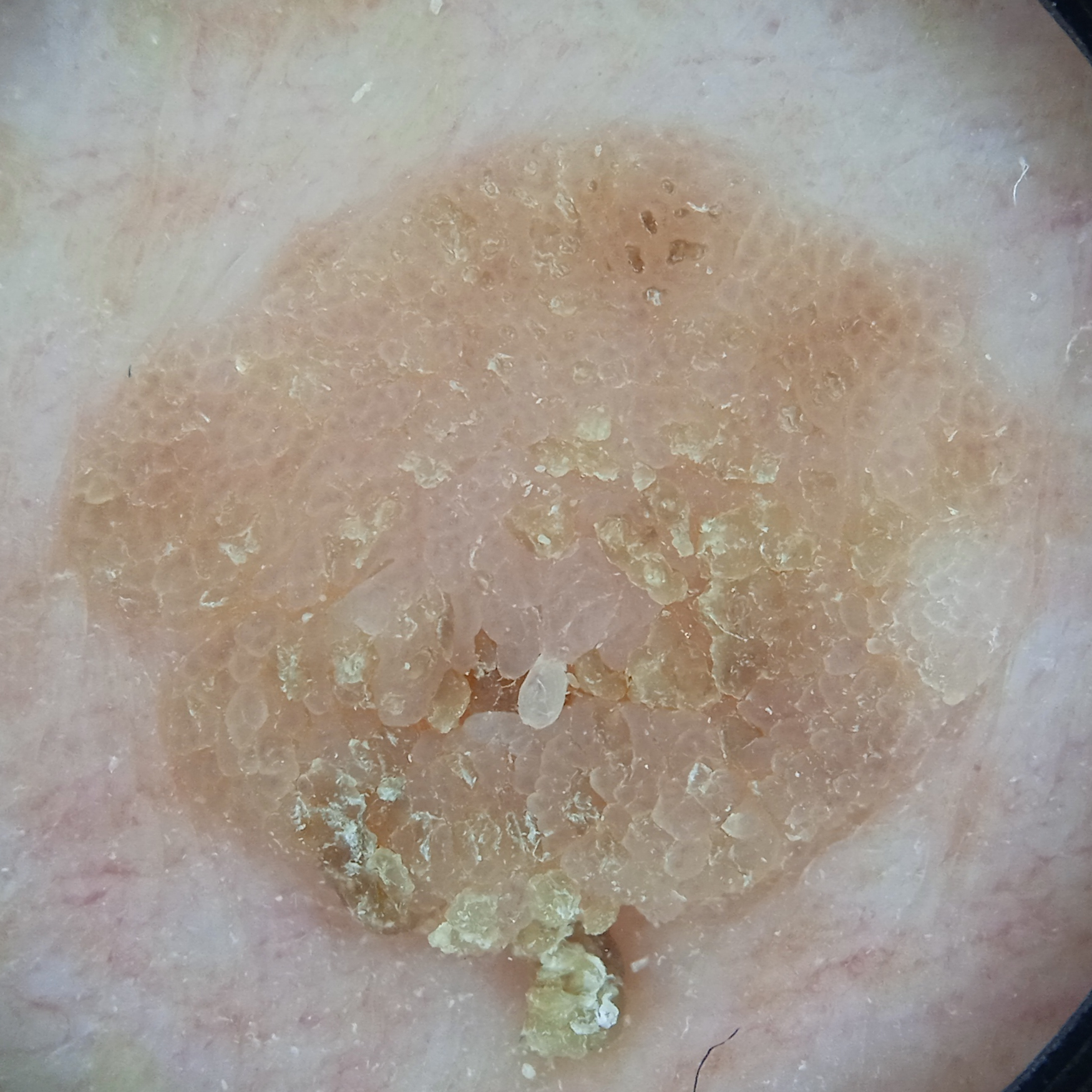Case:
– referral — research study (no referral diagnosis)
– image type — dermatoscopic image
– subject — male, 62 years of age
– anatomic site — the torso
– diameter — 11.3 mm
– assessment — seborrheic keratosis (dermatologist consensus)